Dermoscopy of a skin lesion.
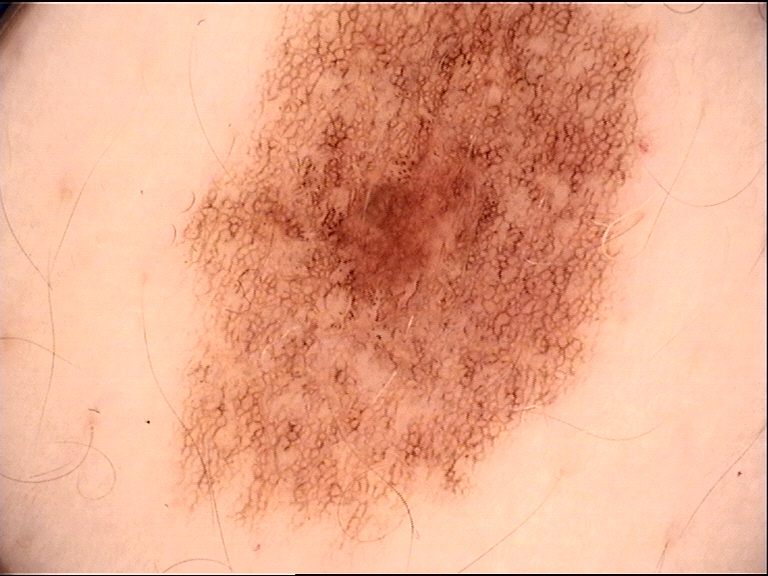Classified as a dysplastic junctional nevus.